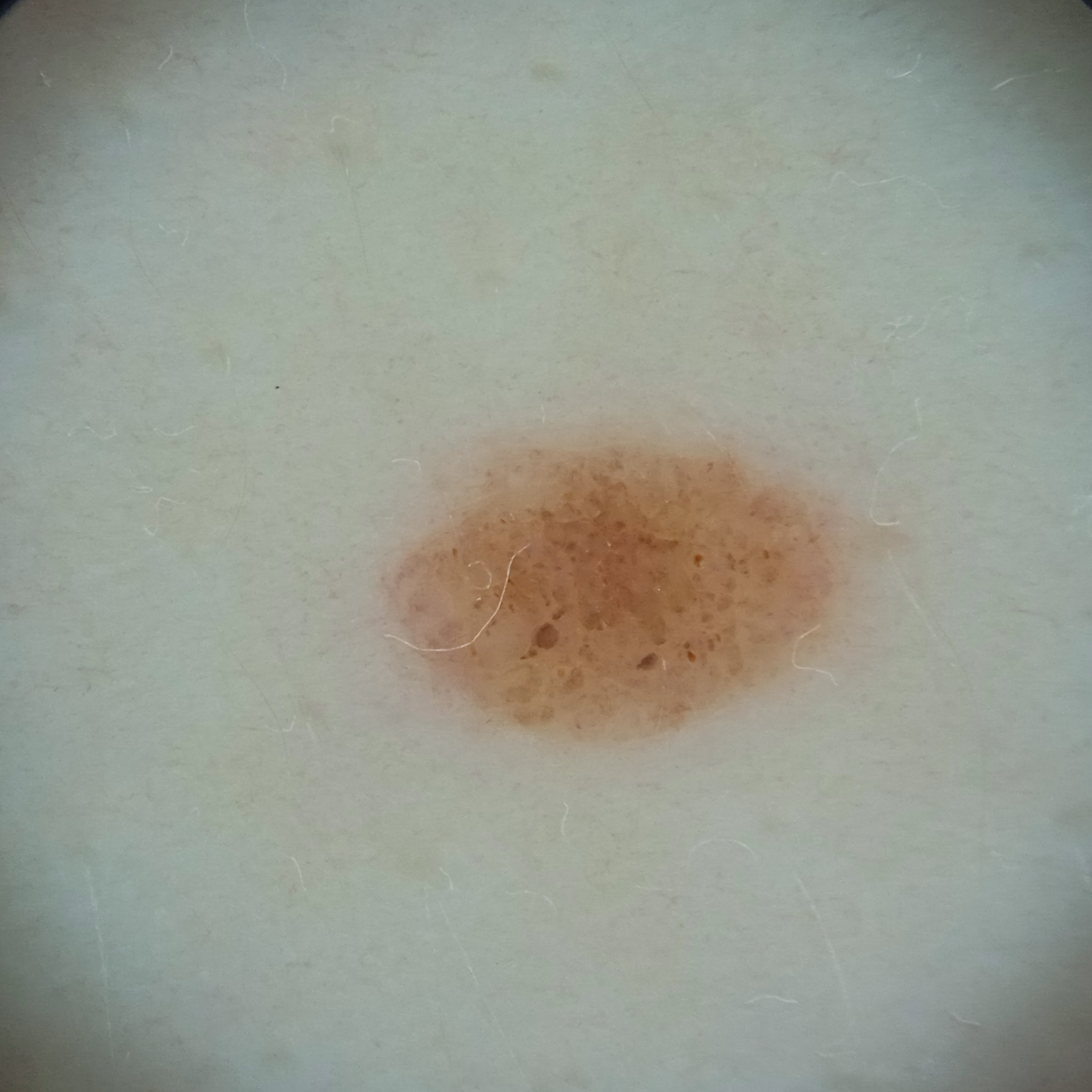A female subject 26 years of age. Collected as part of a research study, without a referral diagnosis. A skin lesion imaged with a dermatoscope. Located on the torso. The lesion measures approximately 5.3 mm. The four-dermatologist consensus diagnosis was a melanocytic nevus.